Fitzpatrick phototype II · a clinical photograph showing a skin lesion · the chart records prior malignancy (patient or family).
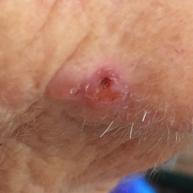lesion_location: the face
diagnosis:
  name: basal cell carcinoma
  code: BCC
  malignancy: malignant
  confirmation: histopathology